An image taken at an angle. The arm is involved. Female subject, age 18–29: 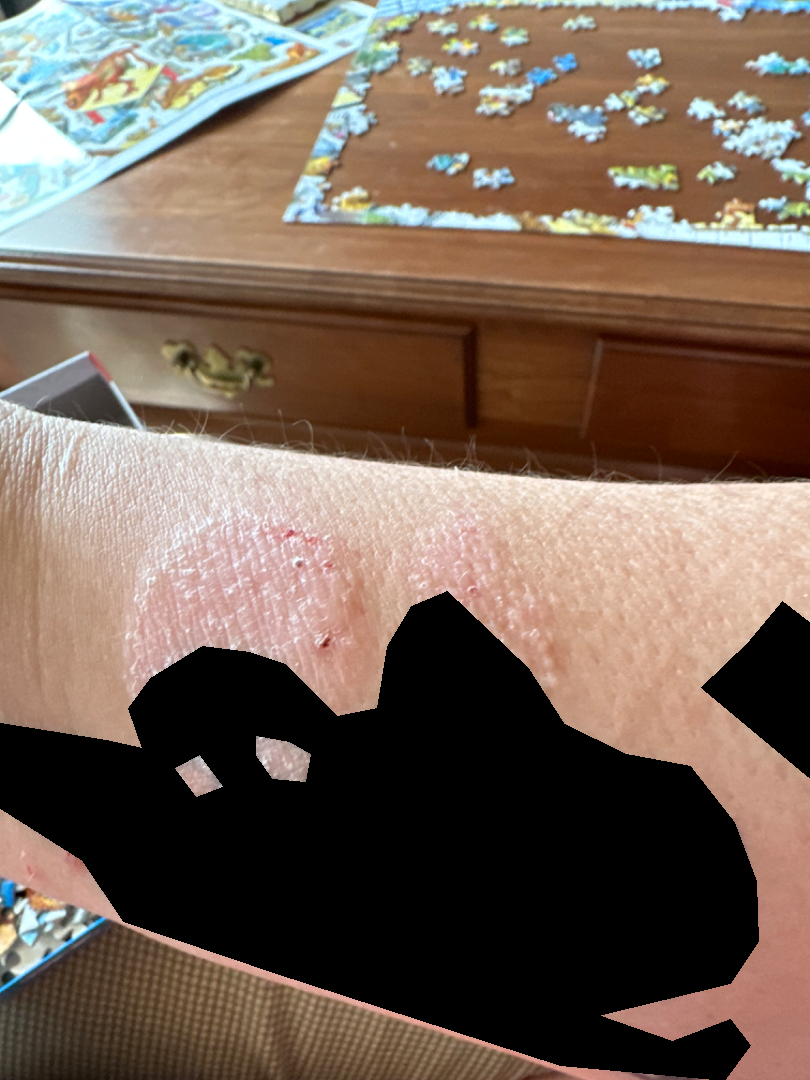Impression:
Psoriasis (69%); Eczema (21%); Tinea (10%).